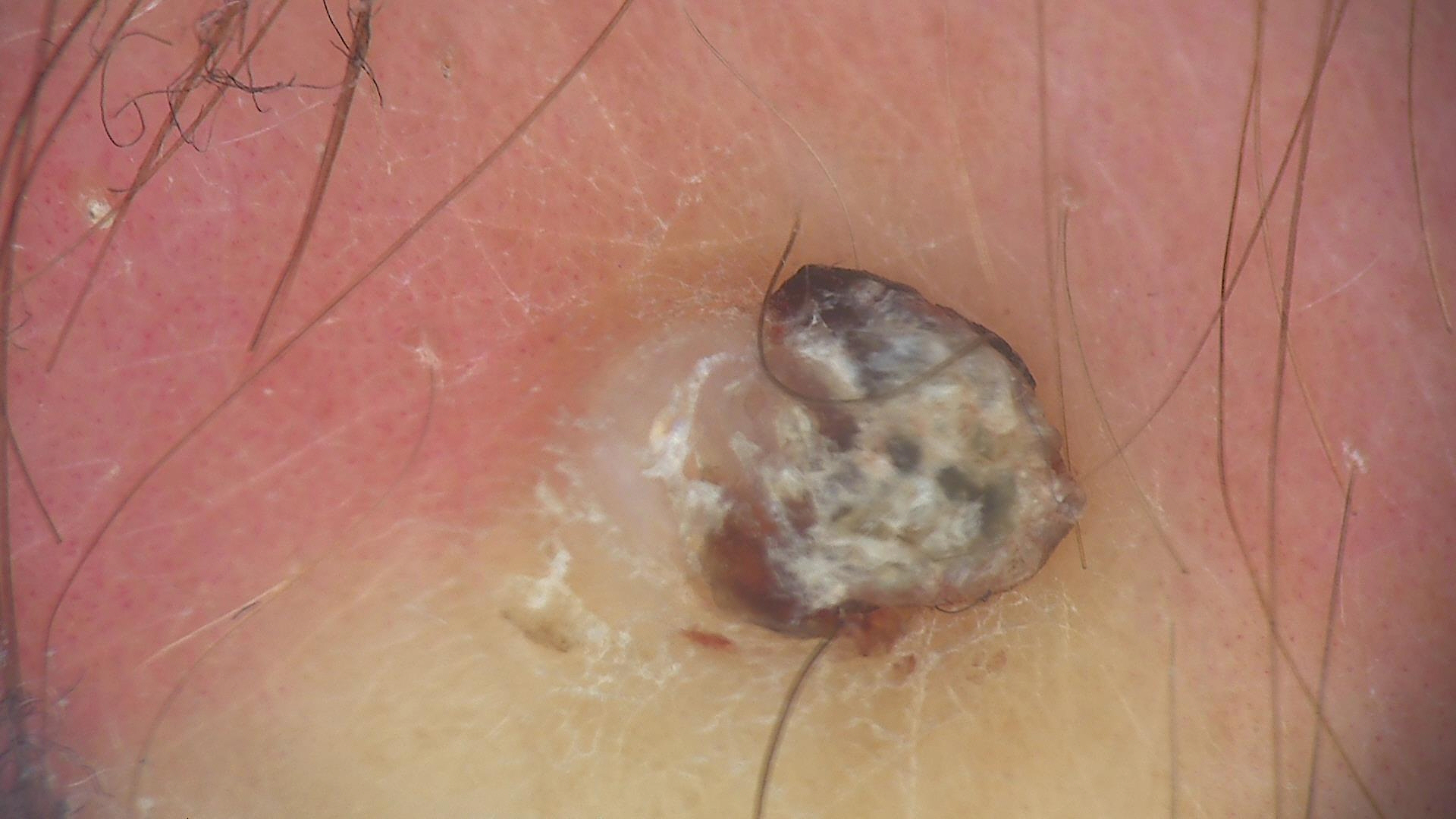Dermoscopy of a skin lesion.
The architecture is that of a keratinocytic lesion.
Biopsy-confirmed as a skin cancer — a squamous cell carcinoma.